A male patient aged around 80 — 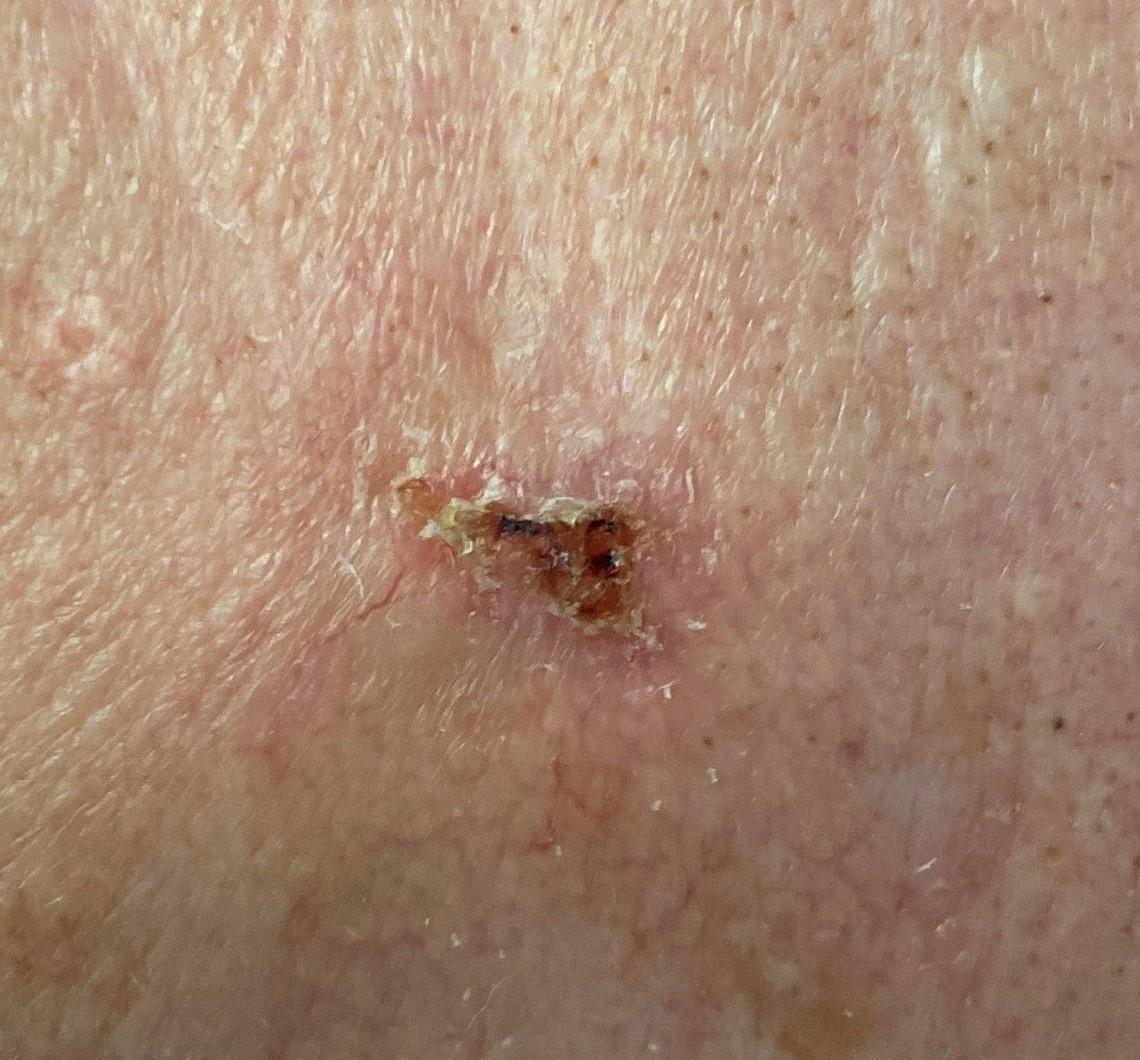* site · the head or neck
* pathology · Basal cell carcinoma (biopsy-proven)